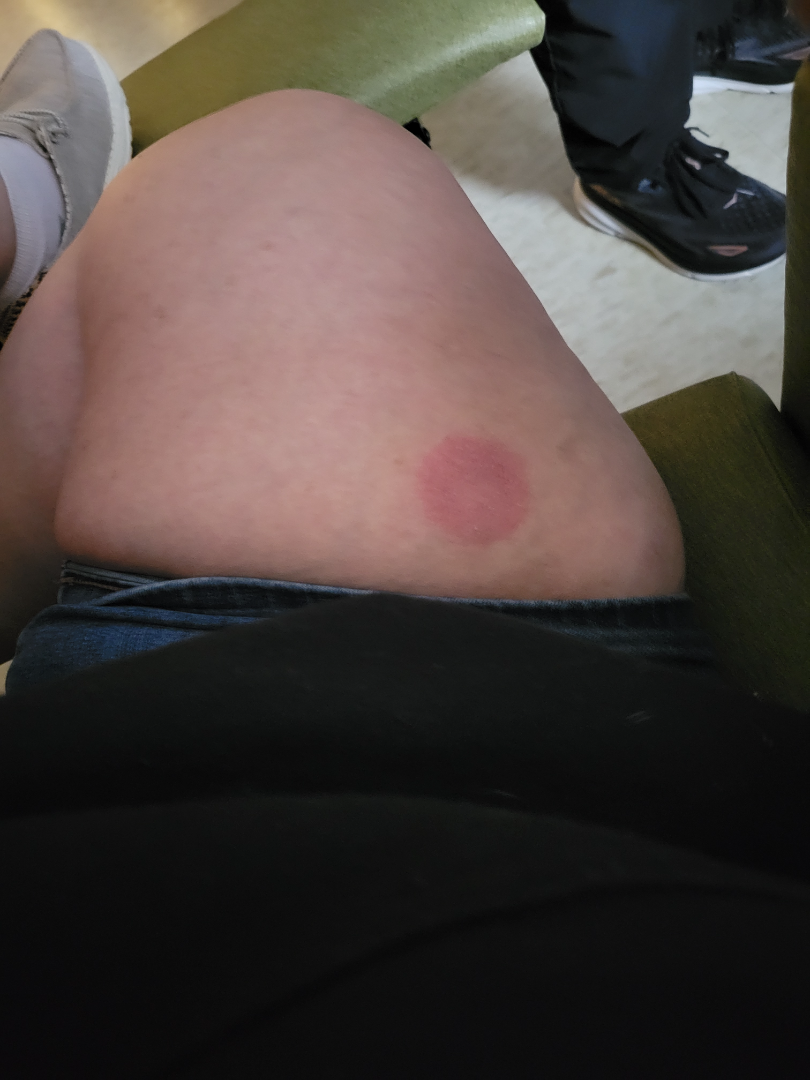The contributor is 50–59, female.
The photograph was taken at a distance.
The affected area is the leg.
On dermatologist assessment of the image, Psoriasis and Cutaneous T Cell Lymphoma were each considered, in no particular order.